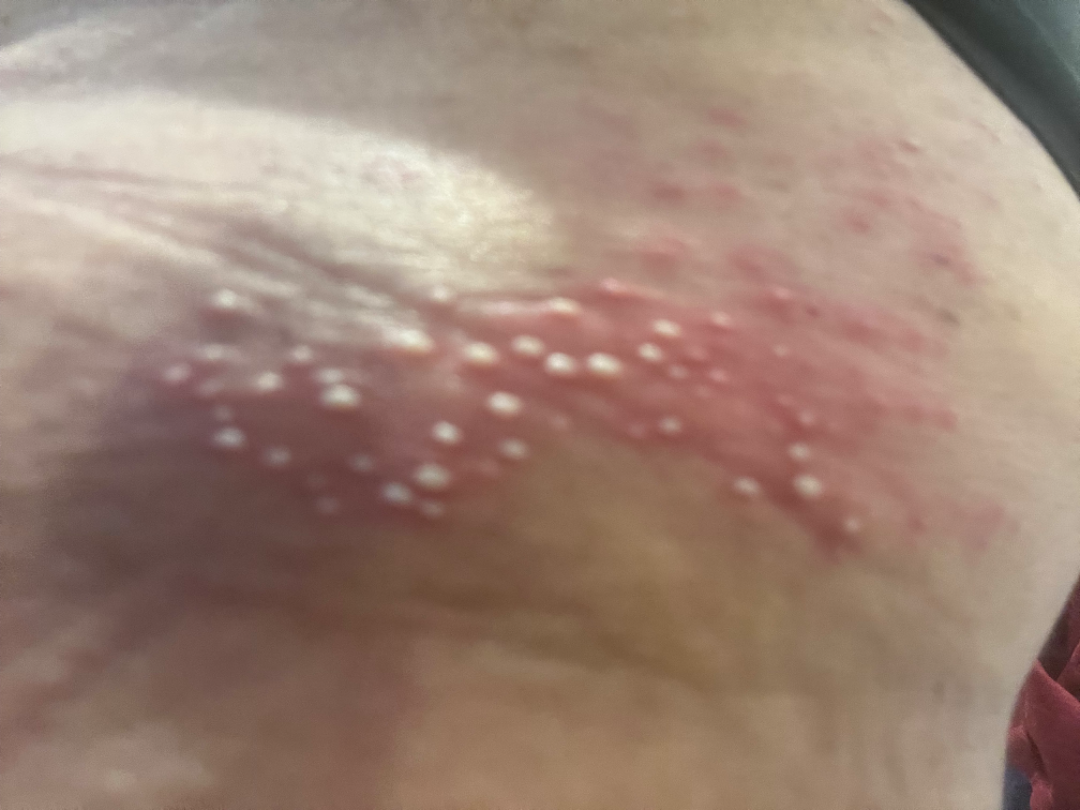{"assessment": "indeterminate", "texture": "raised or bumpy", "duration": "less than one week", "body_site": "front of the torso", "skin_tone": {"fitzpatrick": "III", "fitzpatrick_source": "self_reported", "monk_skin_tone": 2}, "shot_type": "close-up", "patient_category": "a rash", "symptoms": "none reported"}